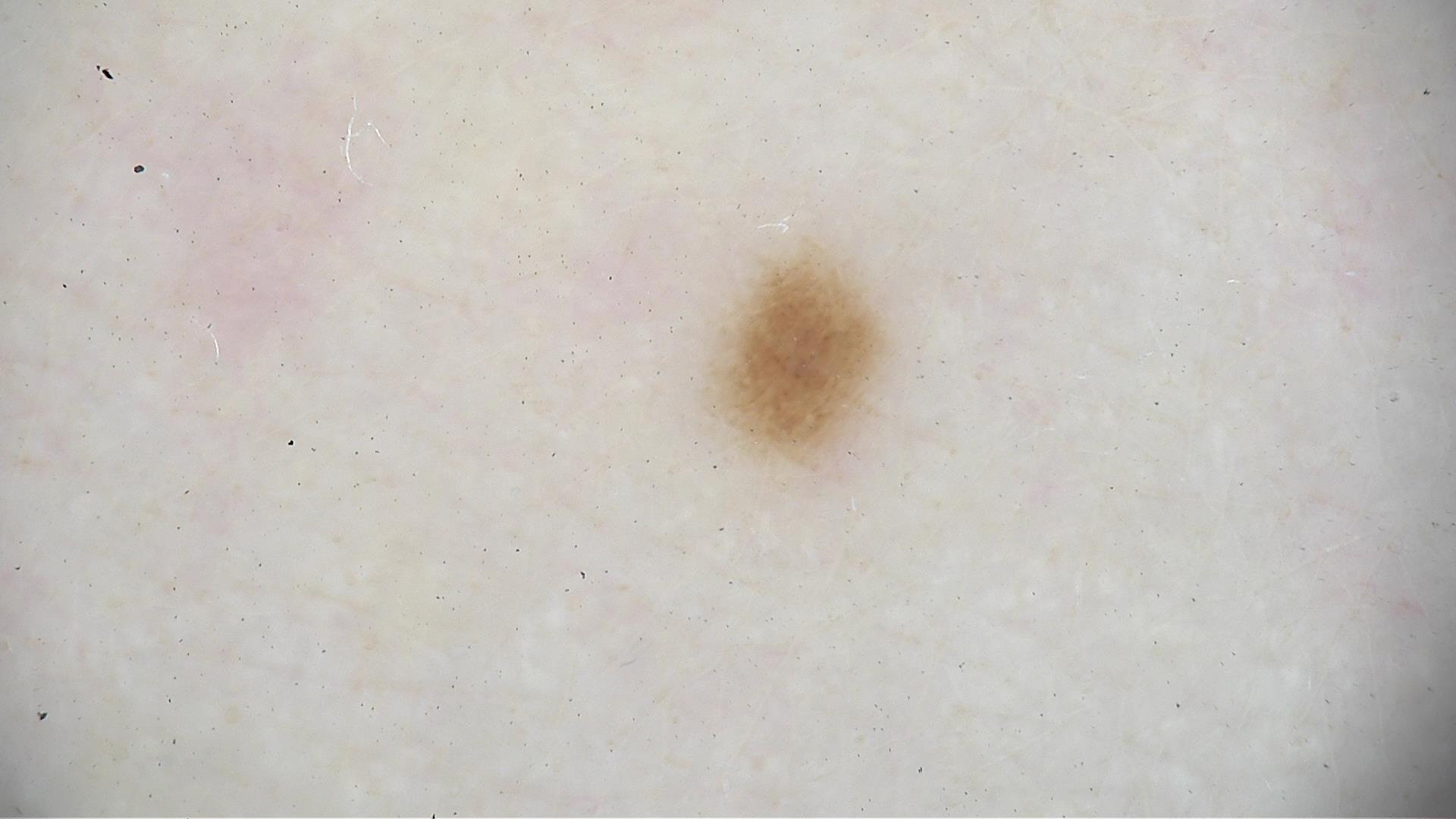{"image": "dermoscopy", "diagnosis": {"name": "junctional nevus", "code": "jb", "malignancy": "benign", "super_class": "melanocytic", "confirmation": "expert consensus"}}